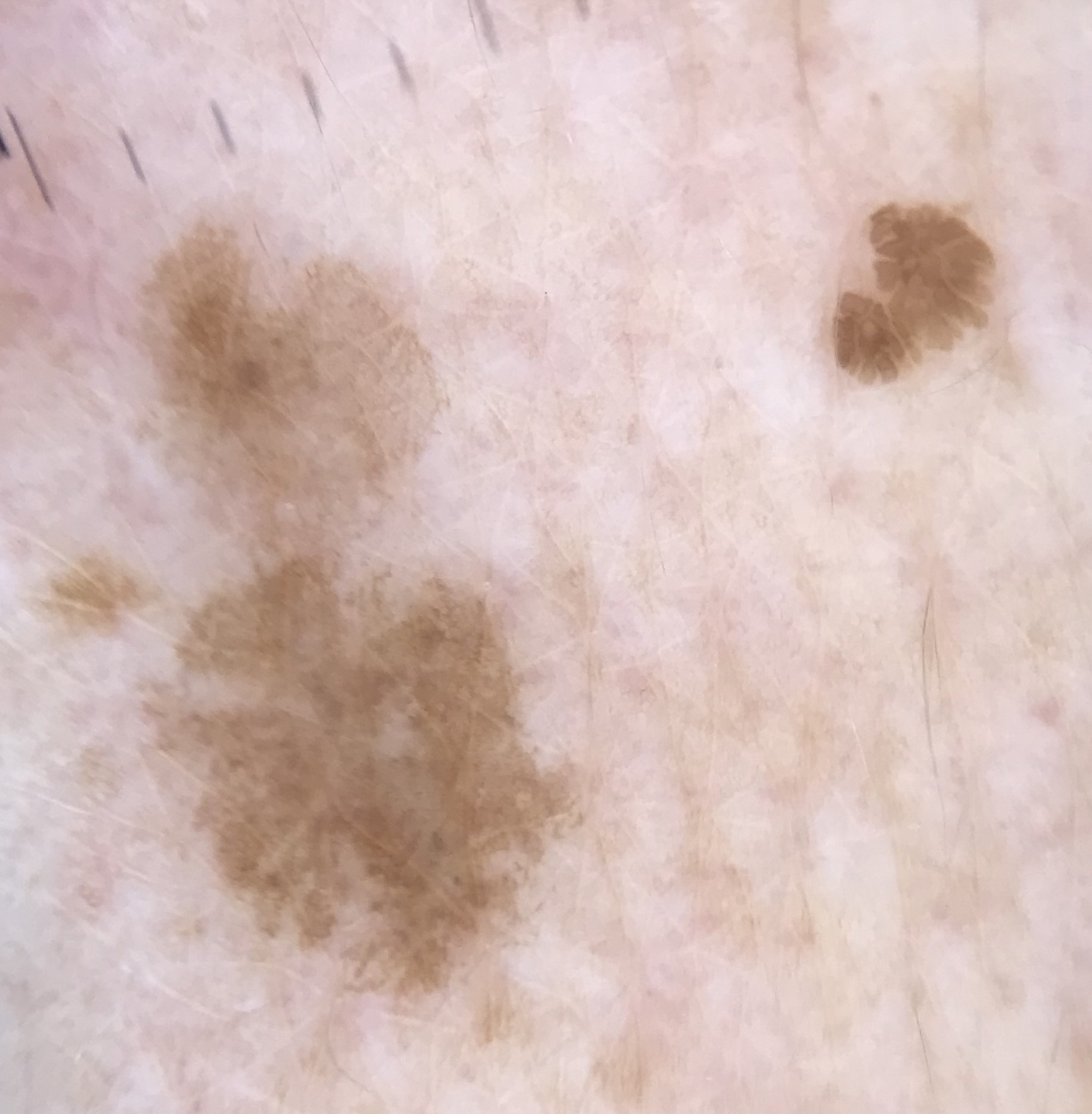A dermoscopic image of a skin lesion.
This is a keratinocytic lesion.
Labeled as a seborrheic keratosis.